A dermoscopic close-up of a skin lesion. A male subject in their mid- to late 40s:
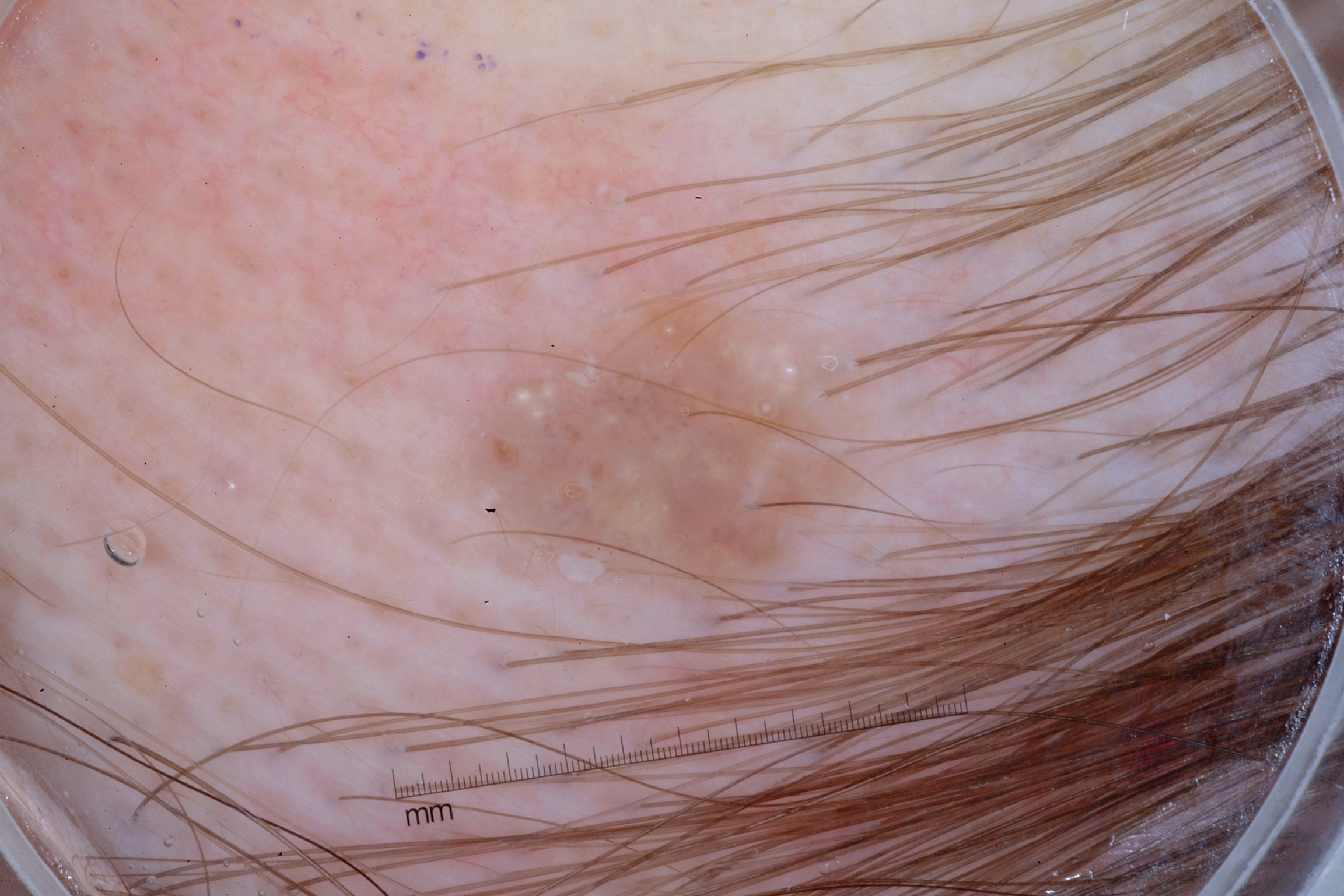Notes:
* lesion location — bbox(419, 279, 895, 615)
* dermoscopic pattern — milia-like cysts; absent: negative network, pigment network, and streaks
* diagnostic label — a seborrheic keratosis